Dermoscopy of a skin lesion:
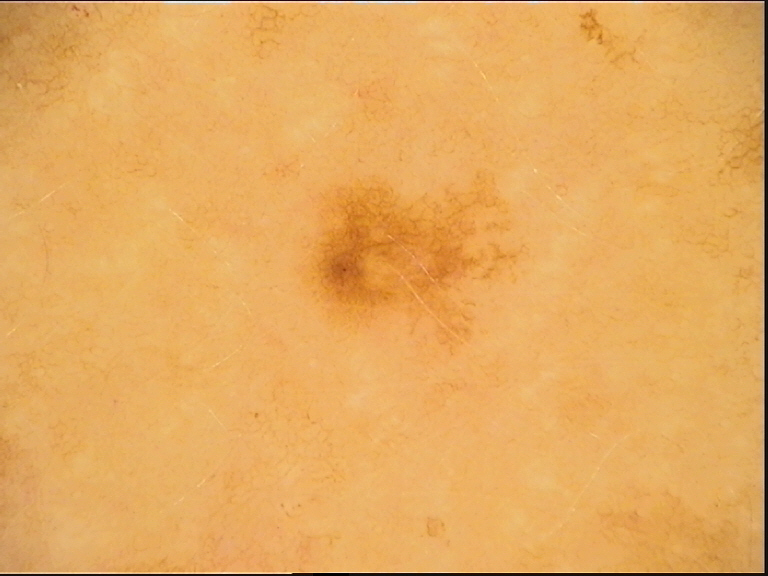{
  "diagnosis": {
    "name": "dysplastic junctional nevus",
    "code": "jd",
    "malignancy": "benign",
    "super_class": "melanocytic",
    "confirmation": "expert consensus"
  }
}